A male patient, aged 48 to 52 · dermoscopy of a skin lesion.
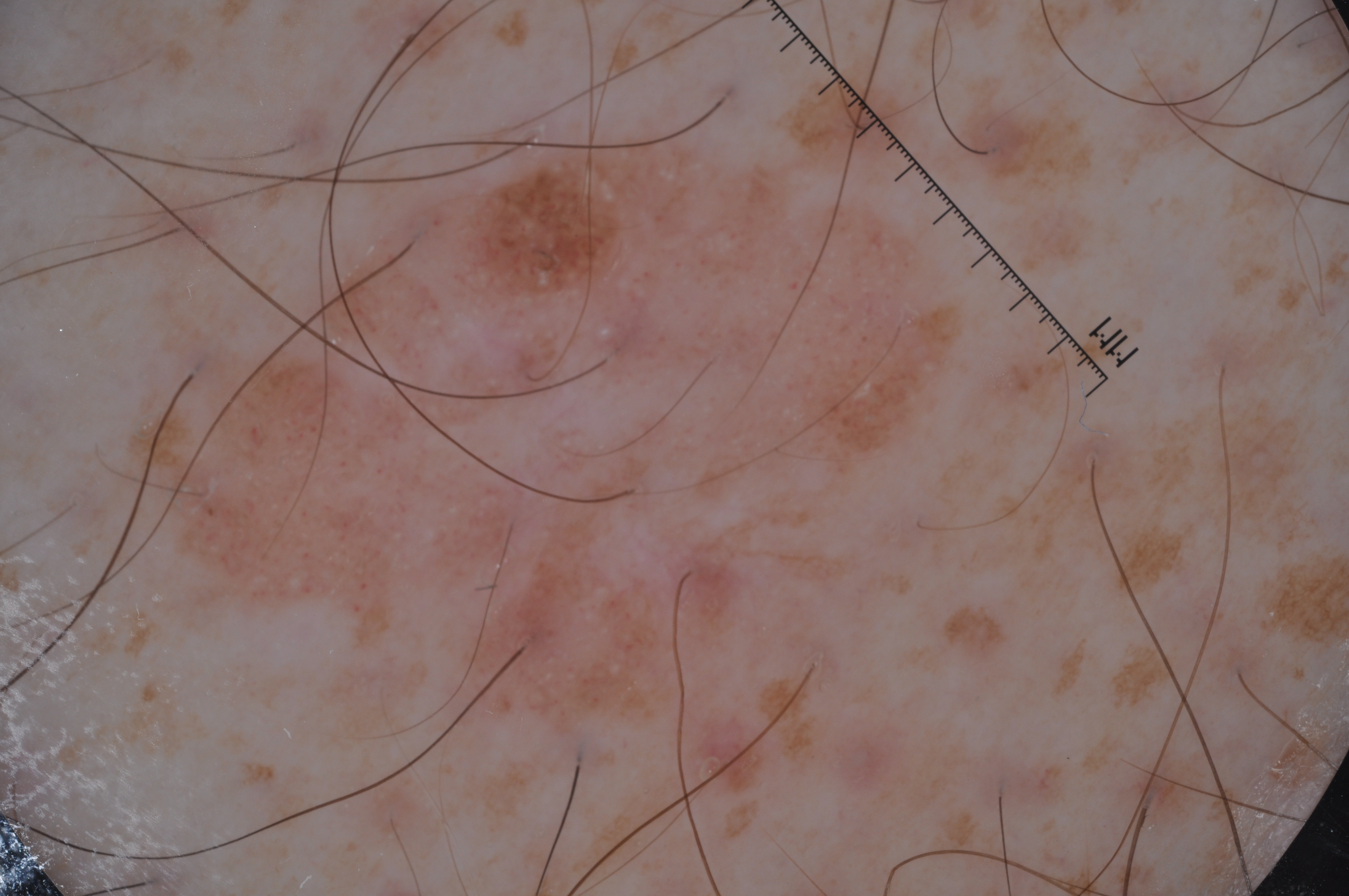{
  "lesion_location": {
    "bbox_xyxy": [
      131,
      137,
      966,
      727
    ]
  },
  "lesion_extent": "moderate",
  "dermoscopic_features": {
    "present": [
      "pigment network",
      "milia-like cysts"
    ],
    "absent": [
      "negative network",
      "streaks"
    ]
  },
  "diagnosis": {
    "name": "seborrheic keratosis",
    "malignancy": "benign",
    "lineage": "keratinocytic",
    "provenance": "clinical"
  }
}